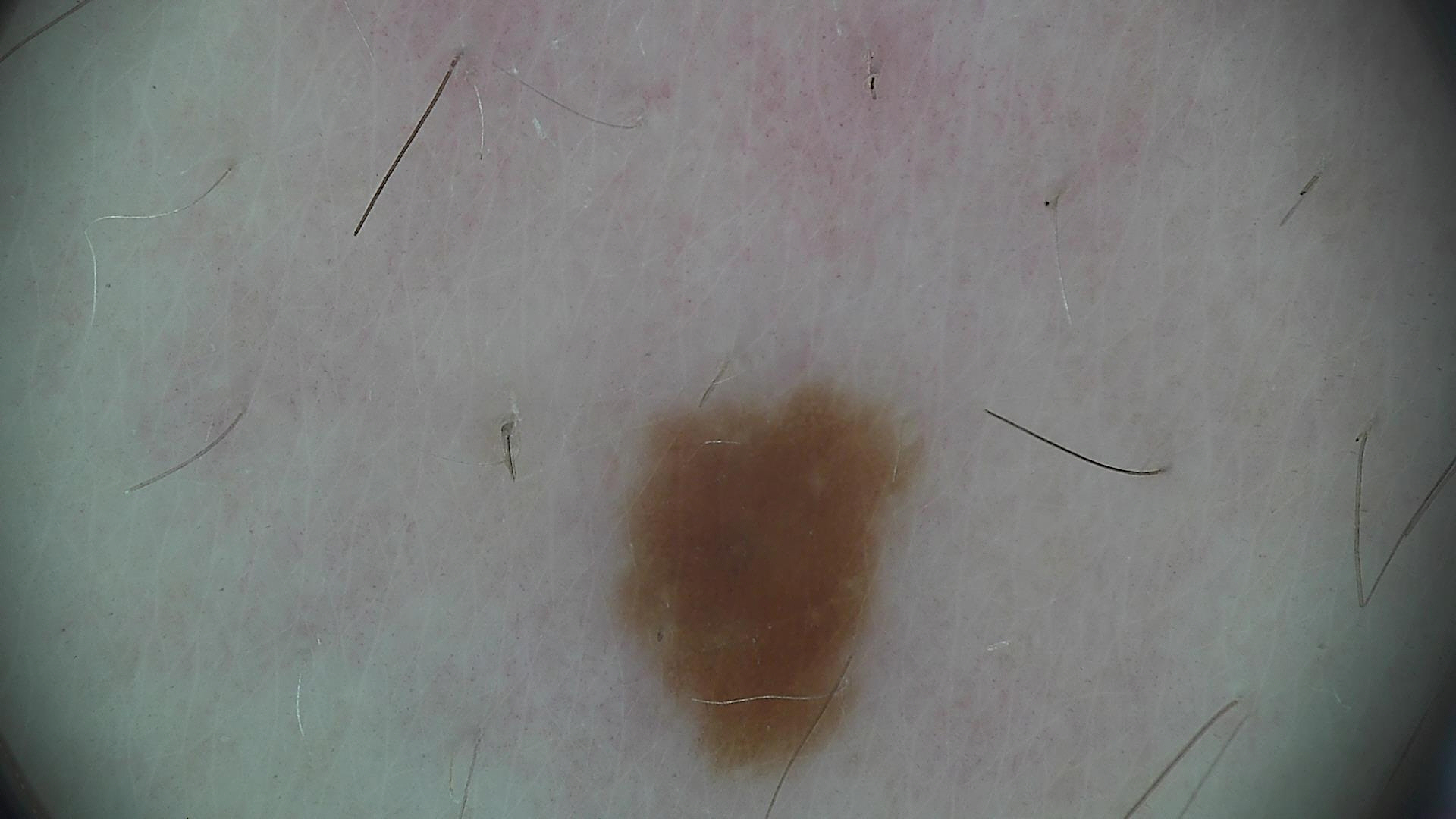class: junctional nevus (expert consensus).